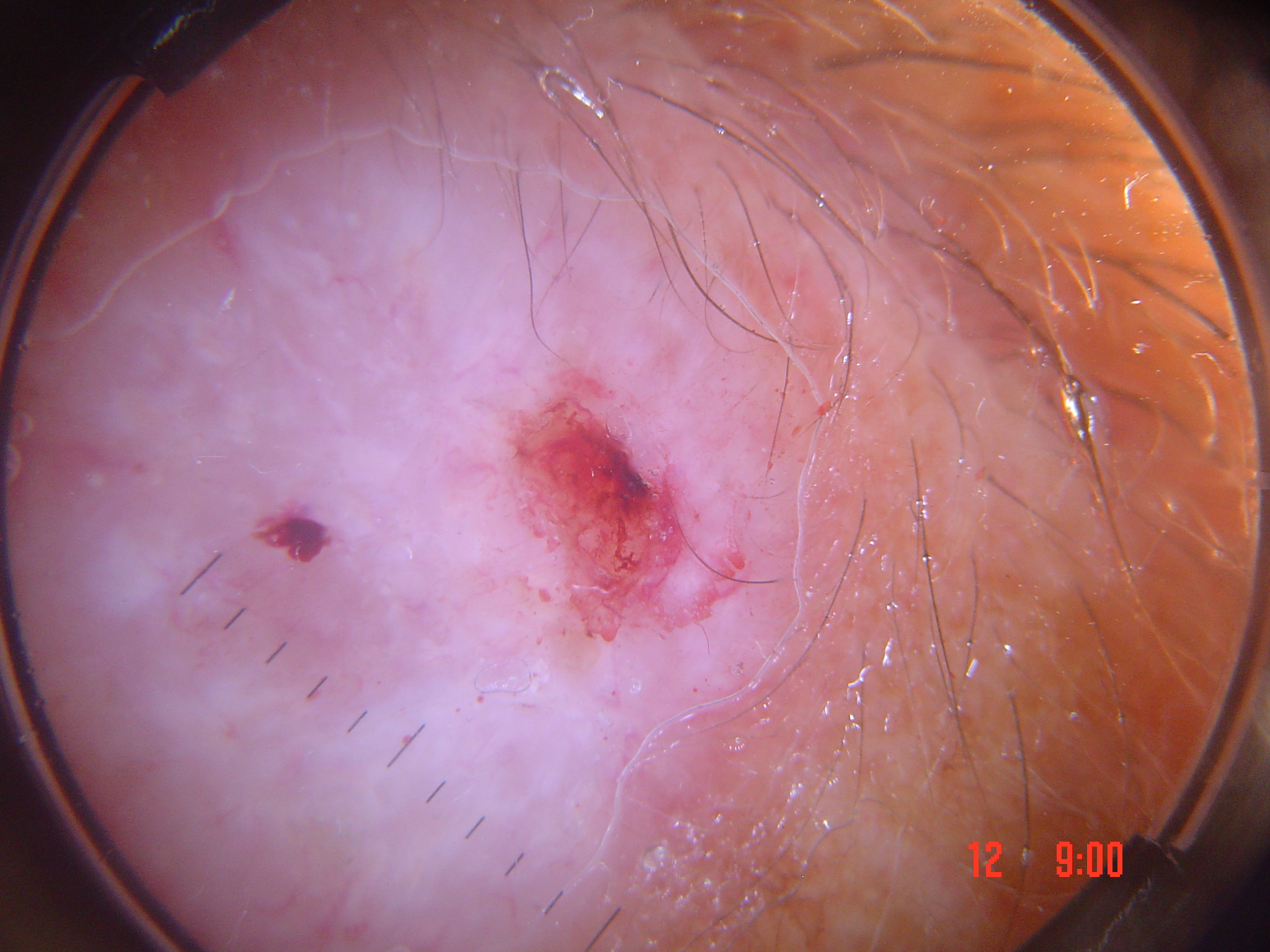diagnosis = basal cell carcinoma (biopsy-proven).